A close-up photograph — 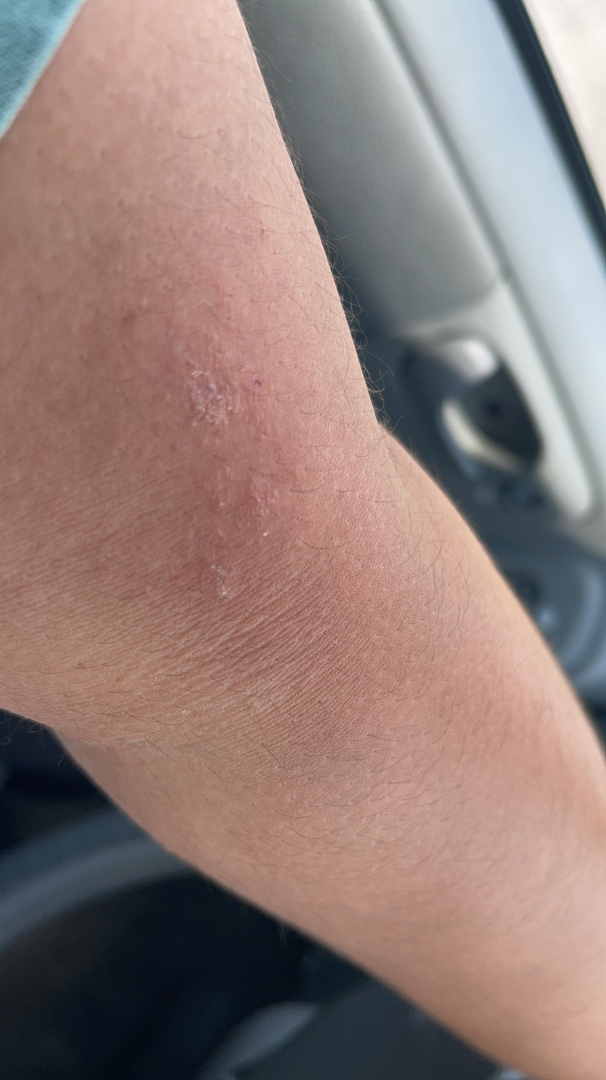Findings:
Single-reviewer assessment: in keeping with Acute and chronic dermatitis.